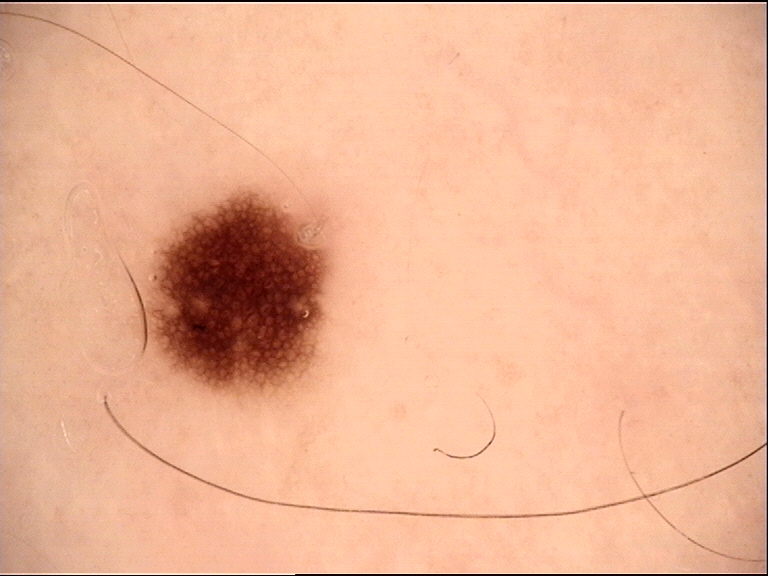modality=dermatoscopy
class=dysplastic junctional nevus (expert consensus)